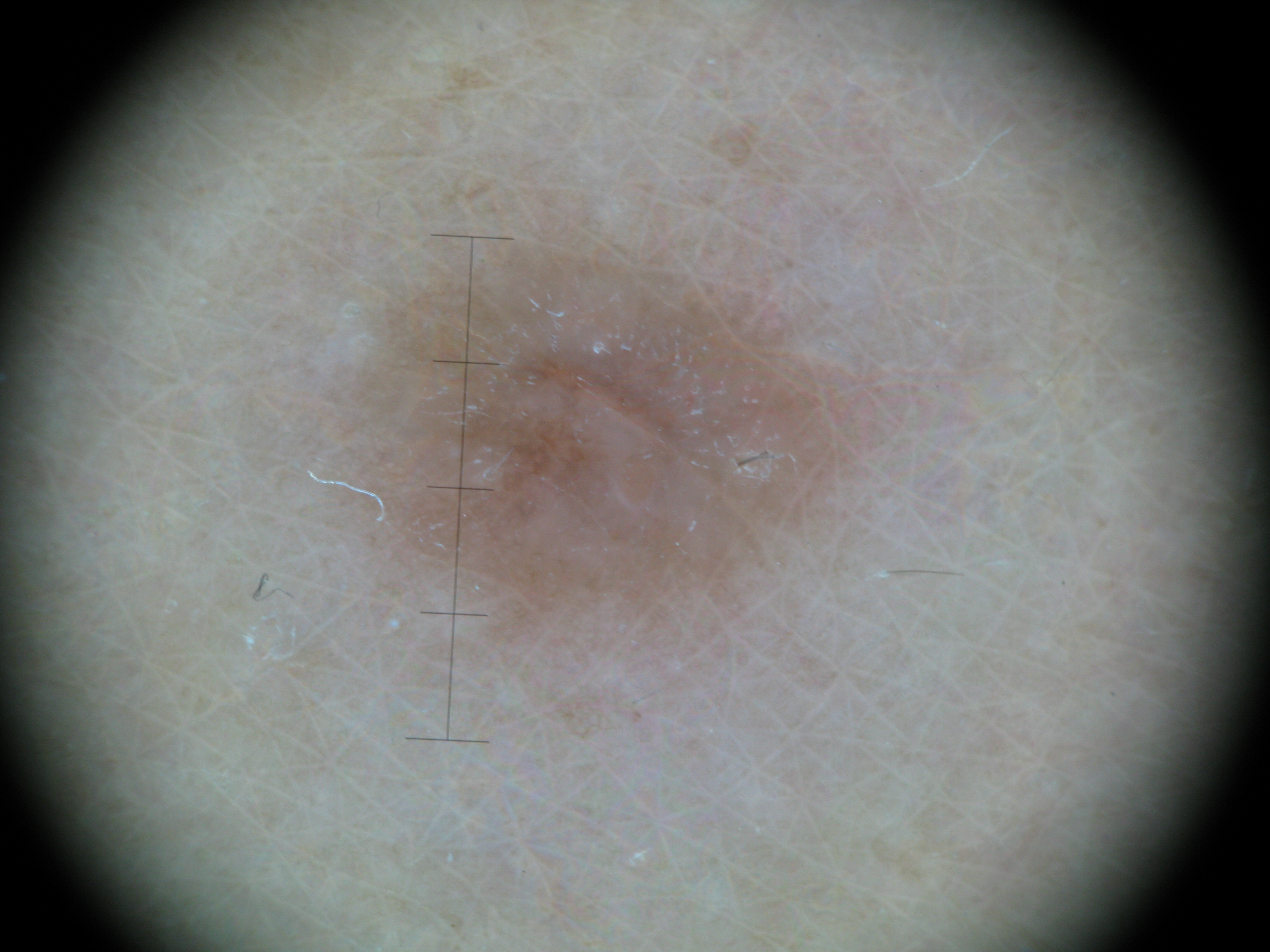image type: dermatoscopy
class: dermatofibroma (expert consensus)